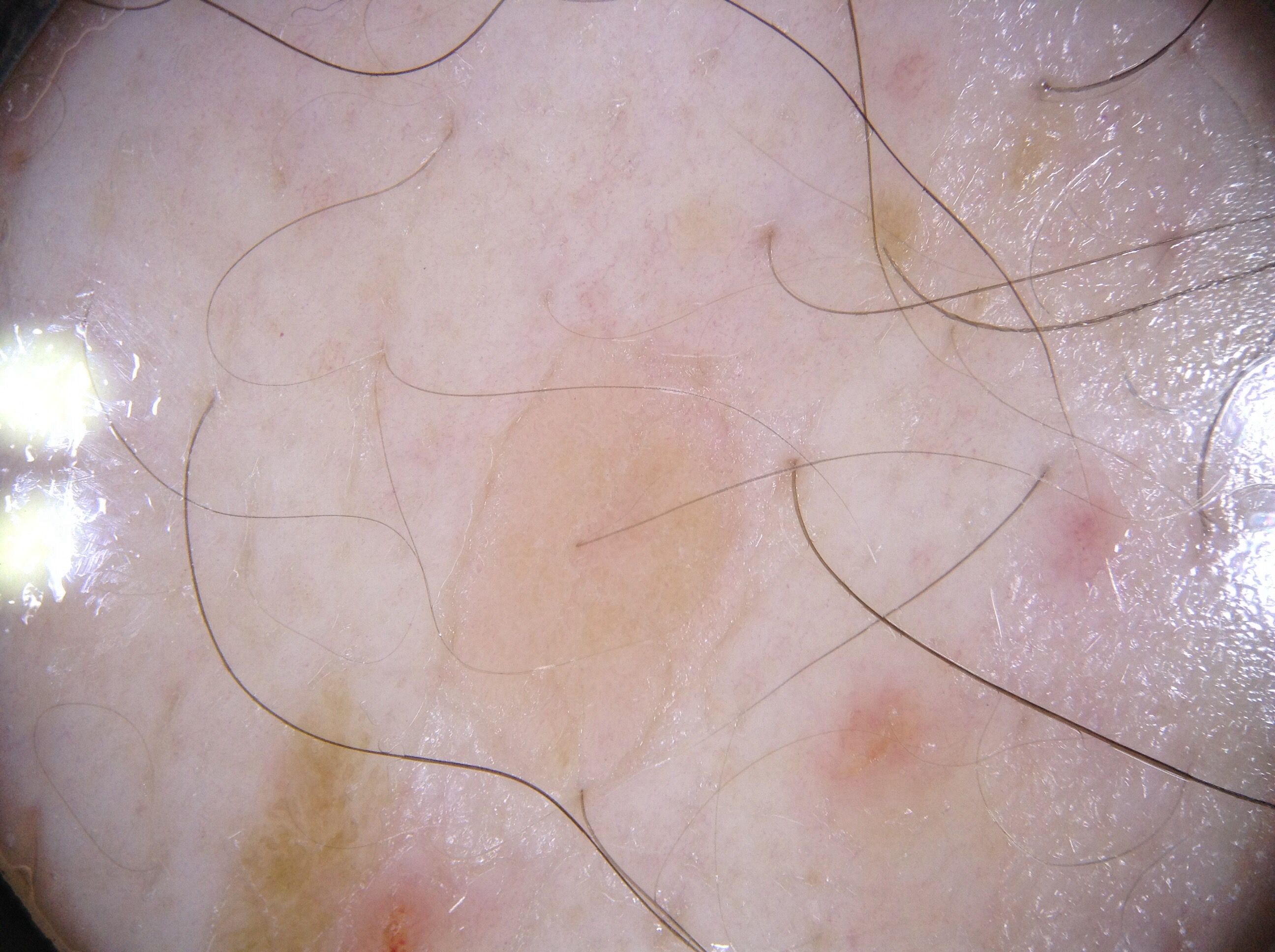image type: dermatoscopic image of a skin lesion
subject: male, roughly 70 years of age
absent dermoscopic features: negative network, milia-like cysts, streaks, and pigment network
bounding box: <bbox>405, 334, 799, 918</bbox>
impression: a seborrheic keratosis, a benign lesion